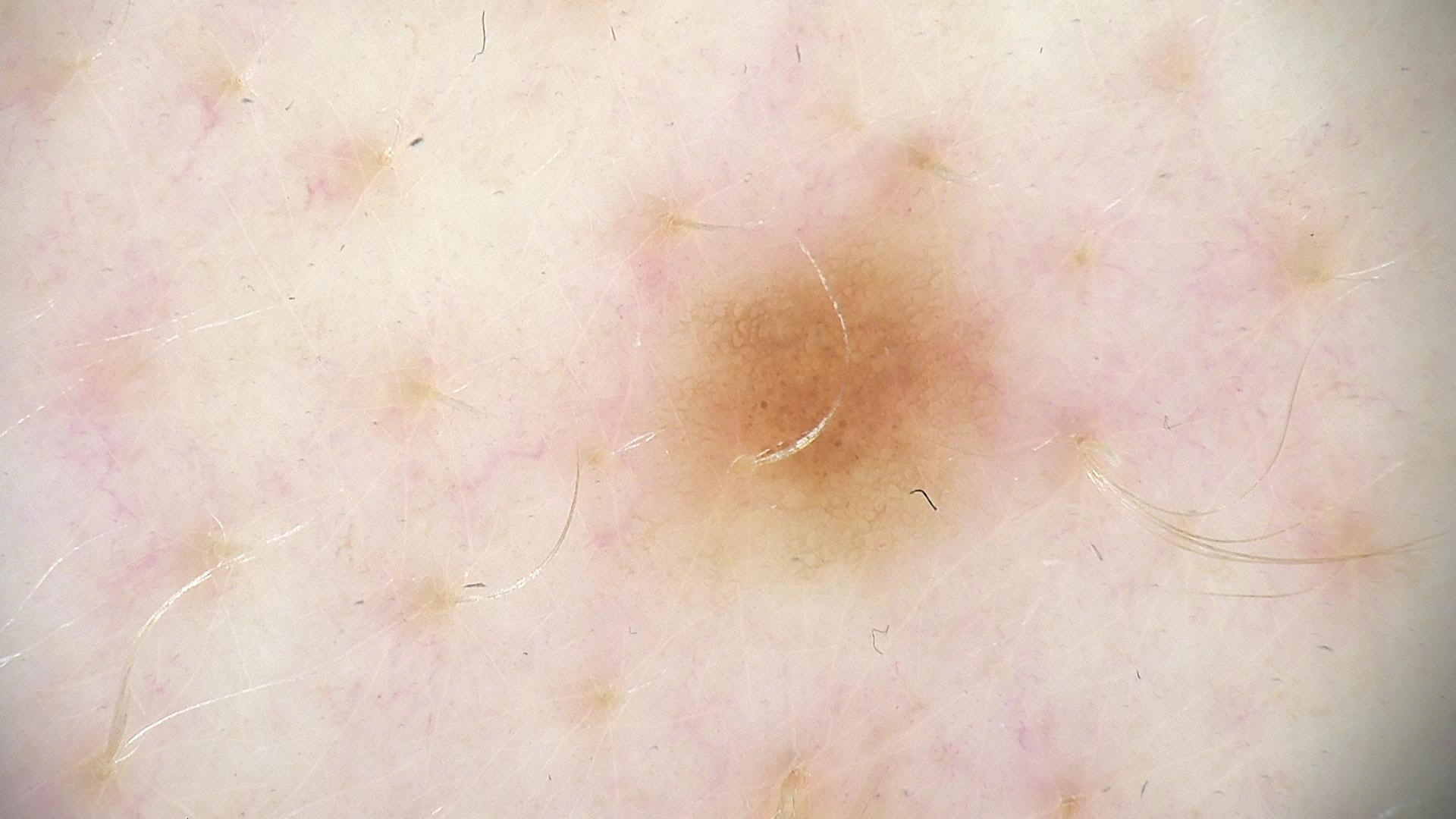The diagnostic label was a benign lesion — a dysplastic junctional nevus.